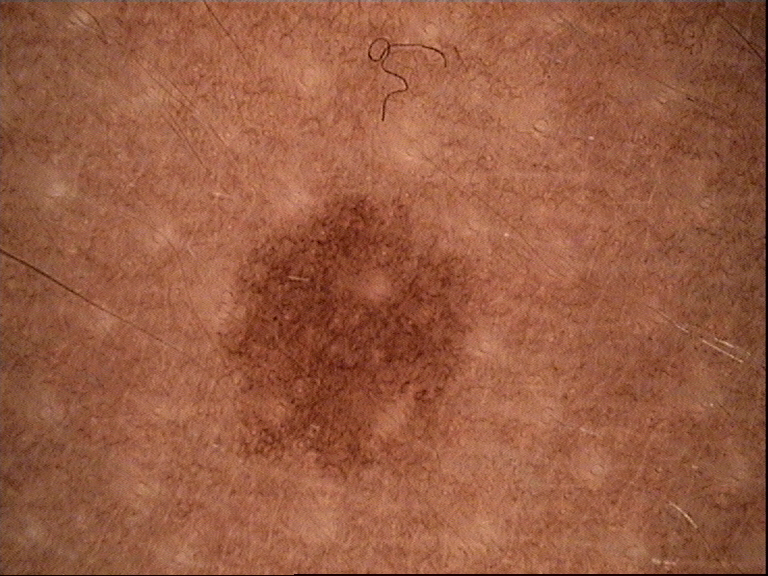Consistent with a junctional nevus.